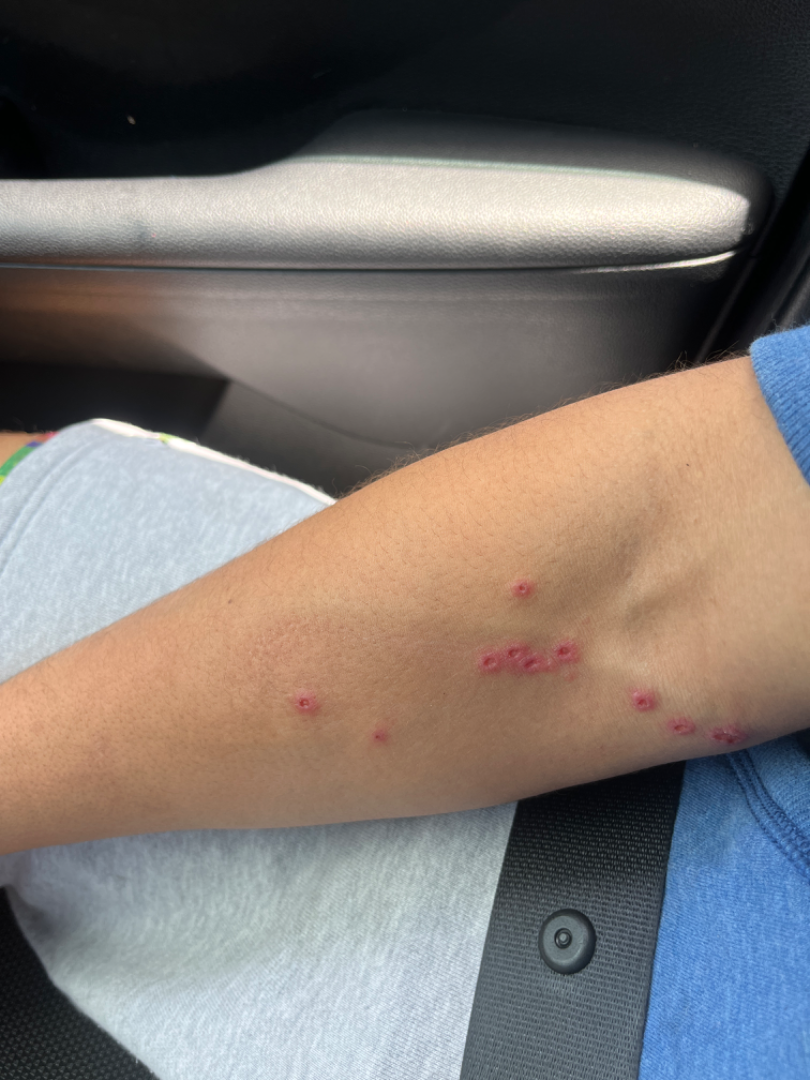Patient information: Reported duration is less than one week. Located on the arm. Skin tone: Fitzpatrick skin type III; human graders estimated Monk Skin Tone 3 or 4. An image taken at a distance. The contributor reports the lesion is raised or bumpy. Review: One reviewing dermatologist: favoring Insect Bite; the differential also includes Herpes Simplex; also raised was Allergic Contact Dermatitis.